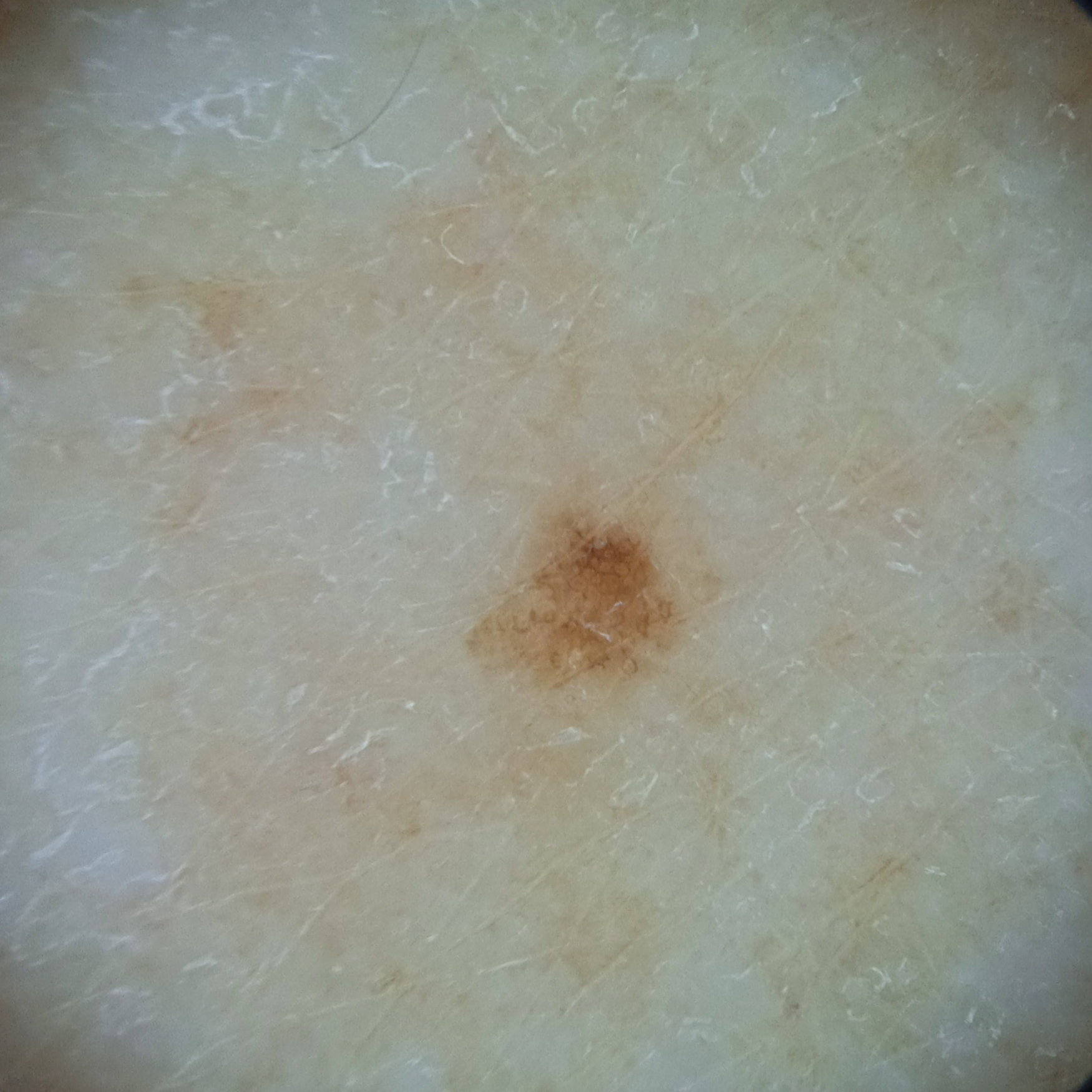diagnostic label: melanocytic nevus (dermatologist consensus).